The arm is involved · an image taken at an angle · female subject, age 18–29 — 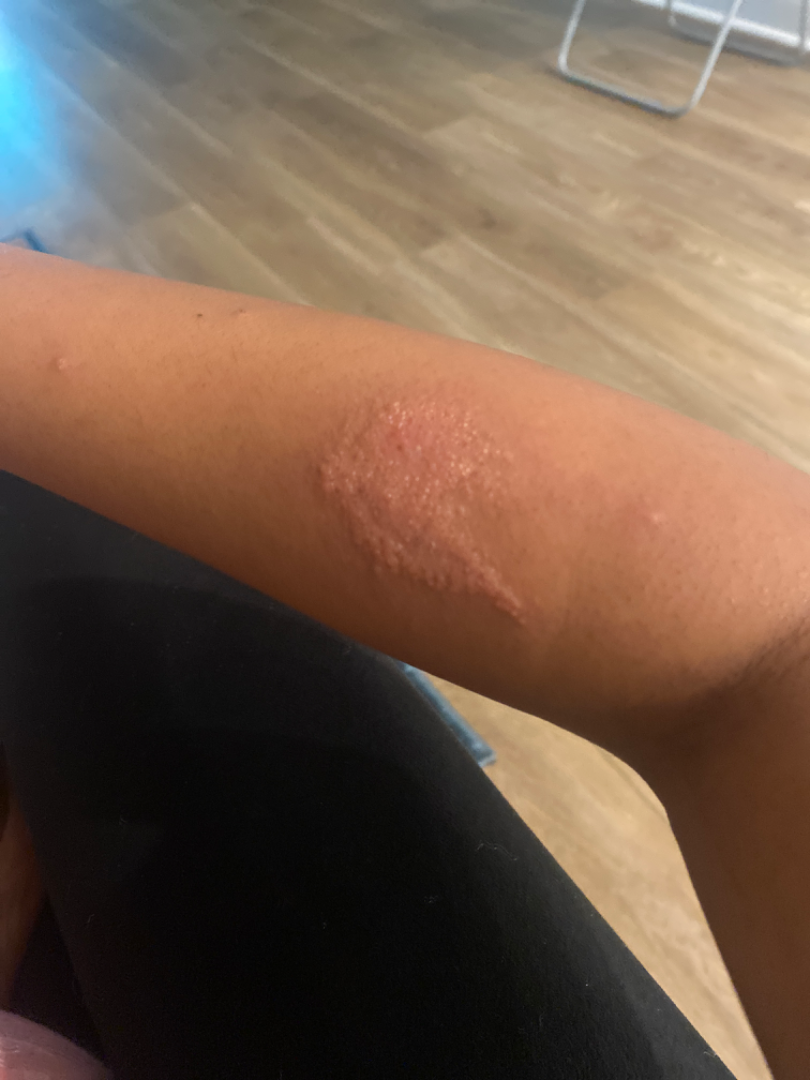Q: What is the differential diagnosis?
A: the impression was split between Impetigo, Psoriasis and Eczema